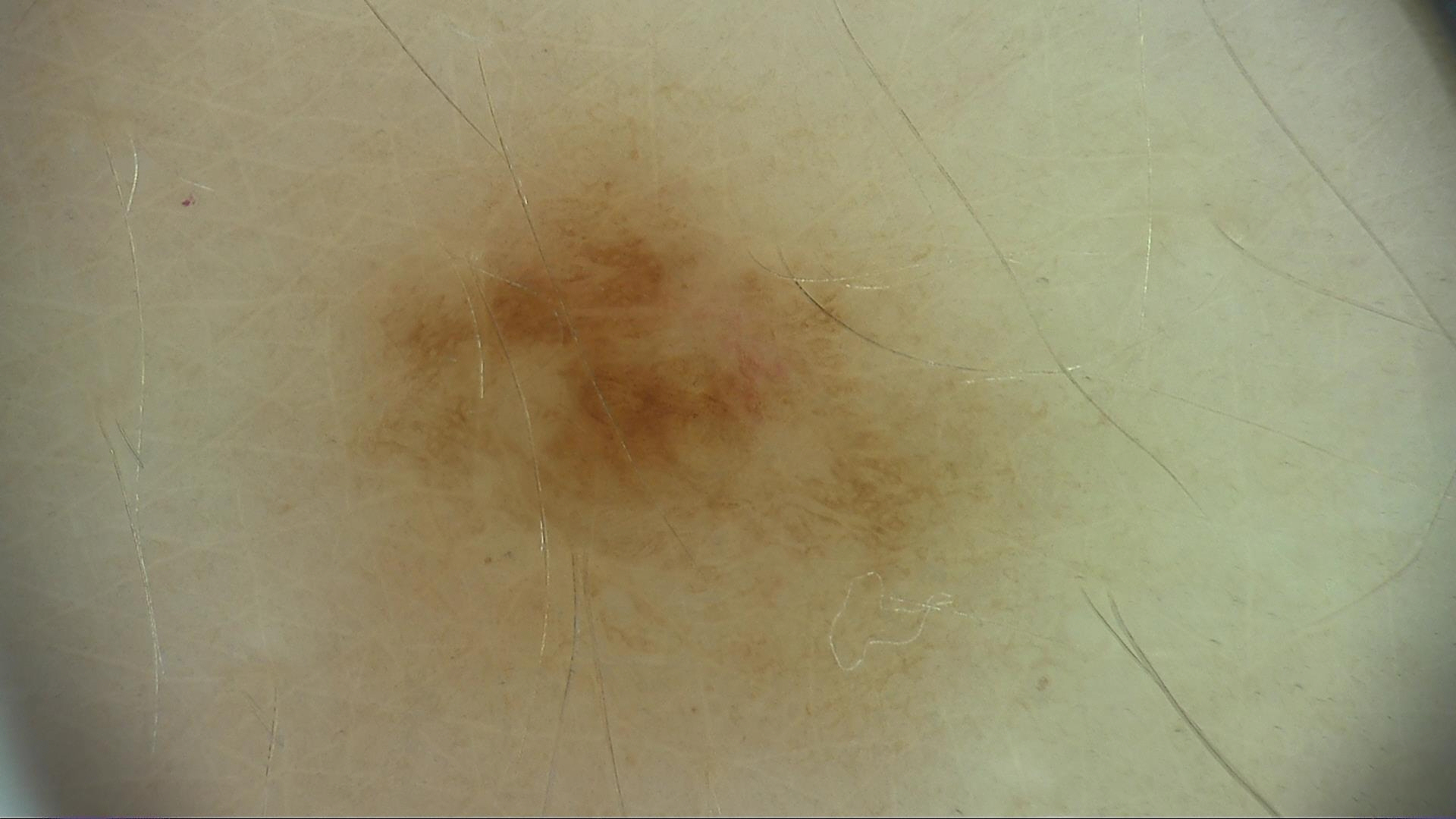A dermatoscopic image of a skin lesion. Labeled as a benign lesion — a dysplastic junctional nevus.